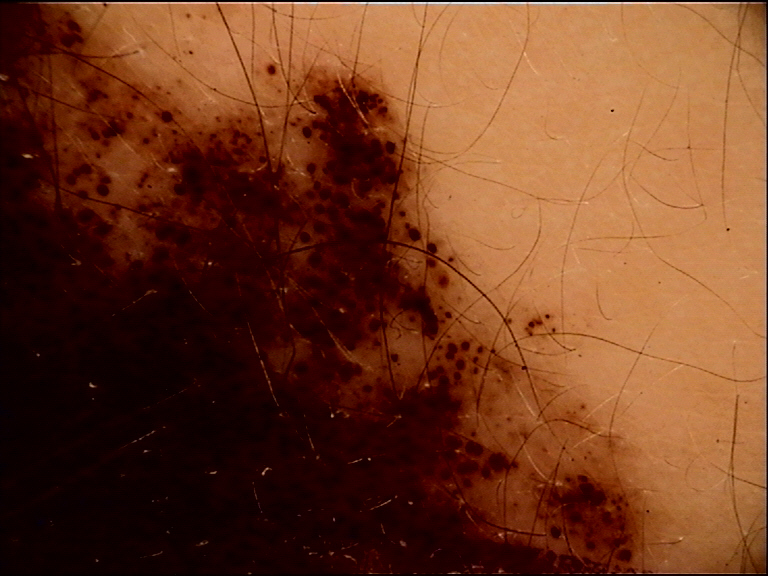<case>
<image>dermoscopy</image>
<lesion_type>
<main_class>banal</main_class>
<pattern>compound</pattern>
</lesion_type>
<diagnosis>
<name>congenital compound nevus</name>
<code>ccb</code>
<malignancy>benign</malignancy>
<super_class>melanocytic</super_class>
<confirmation>expert consensus</confirmation>
</diagnosis>
</case>